Female contributor, age 40–49; the affected area is the arm; the photograph is a close-up of the affected area:
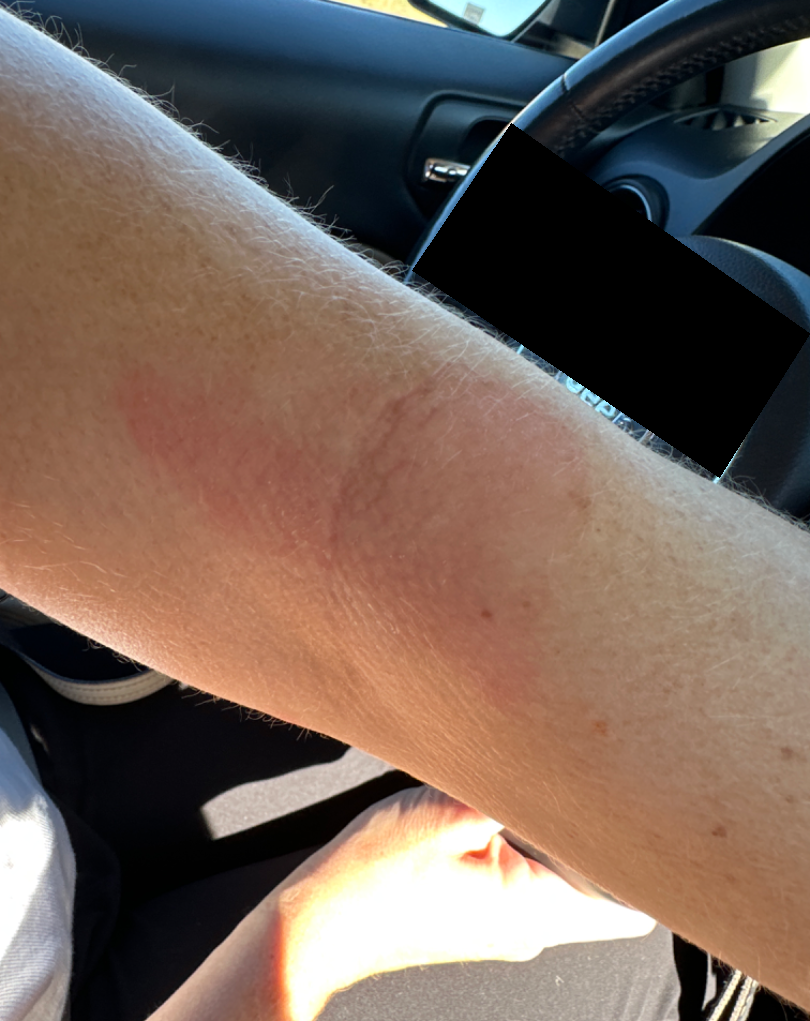  differential:
    Eczema: 0.54
    Allergic Contact Dermatitis: 0.23
    Irritant Contact Dermatitis: 0.23